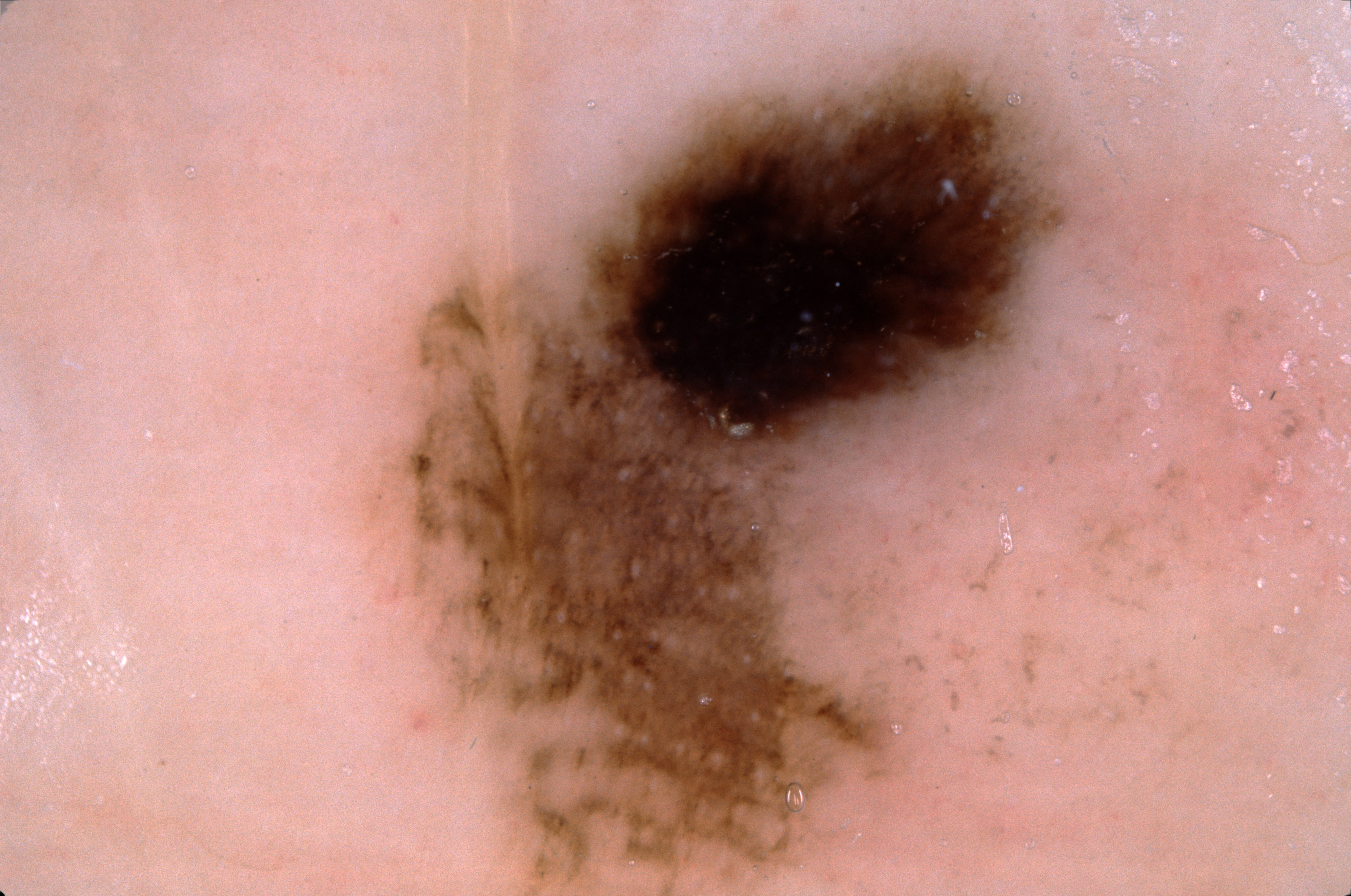{
  "image": {
    "modality": "dermoscopy"
  },
  "lesion_location": {
    "bbox_xyxy": [
      350,
      0,
      1350,
      895
    ]
  },
  "dermoscopic_features": {
    "present": [
      "pigment network"
    ],
    "absent": [
      "streaks",
      "negative network",
      "milia-like cysts"
    ]
  },
  "diagnosis": {
    "name": "melanoma",
    "malignancy": "malignant",
    "lineage": "melanocytic",
    "provenance": "histopathology"
  }
}